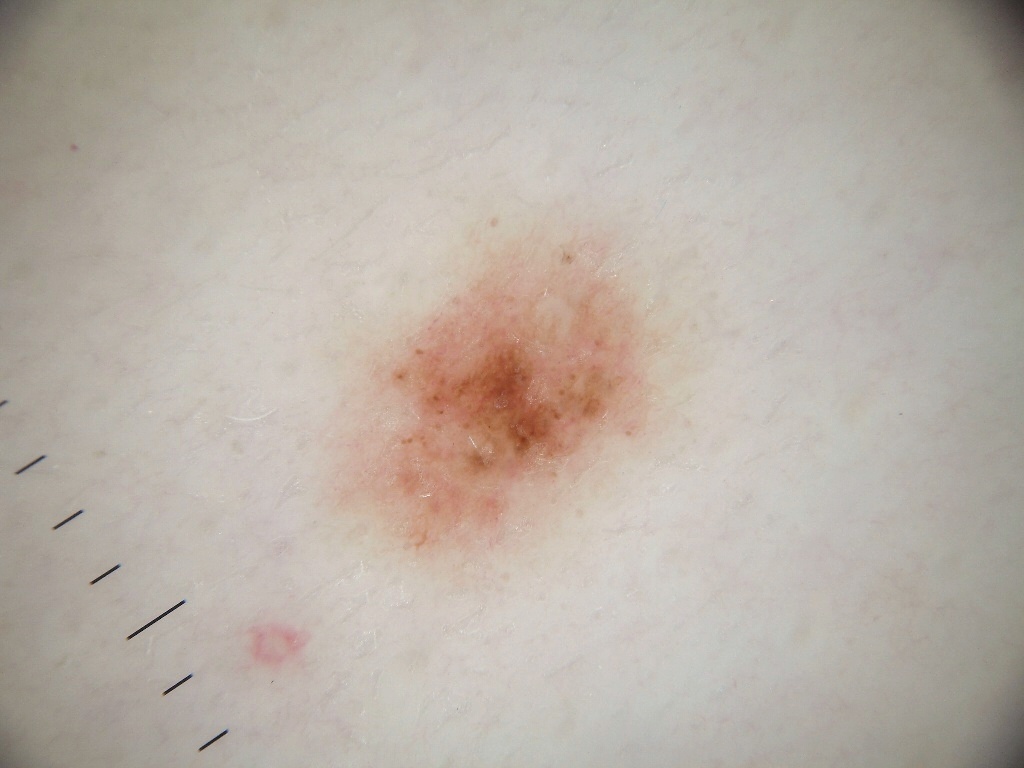A dermoscopic close-up of a skin lesion. The patient is a female approximately 25 years of age. A mid-sized lesion within the field. The lesion occupies the region x1=322 y1=224 x2=686 y2=575. The dermoscopic pattern shows pigment network and globules. Diagnosed as a melanocytic nevus.